A skin lesion imaged with a dermatoscope.
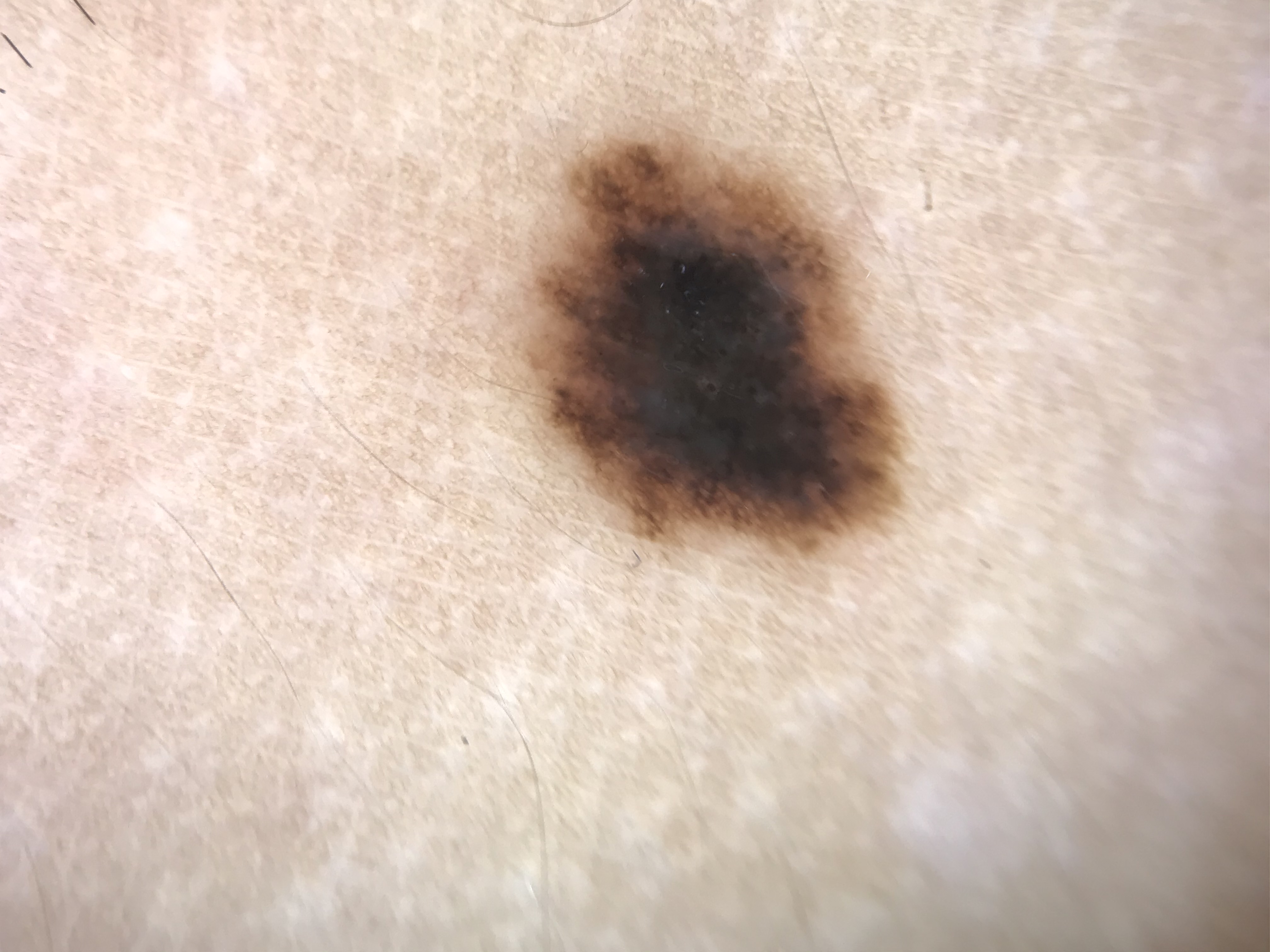Labeled as a benign lesion — a dysplastic junctional nevus.